A dermoscopic image of a skin lesion; FST I; a female subject in their mid- to late 80s or older:
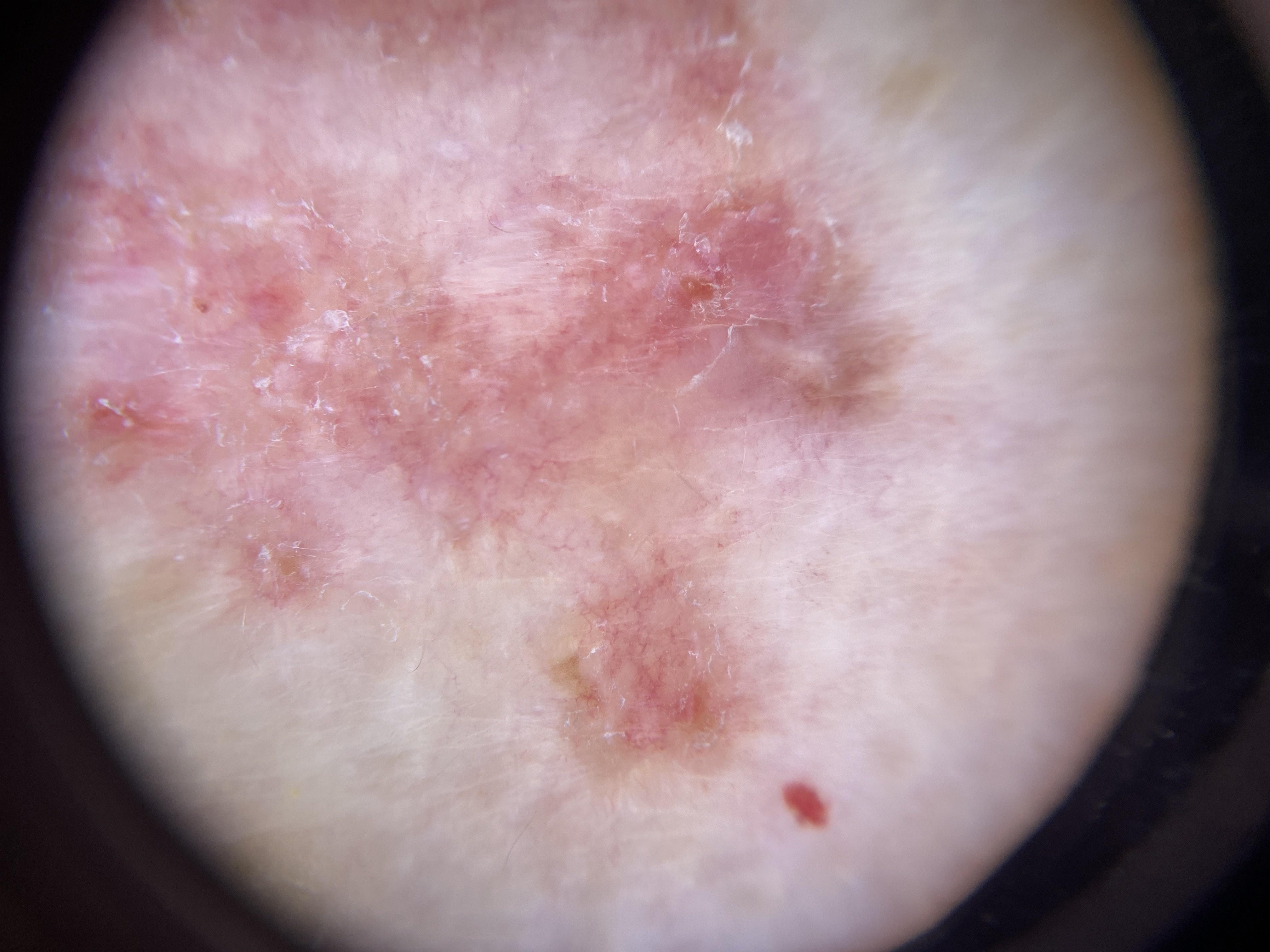Clinical context: The lesion is on an upper extremity. Diagnosis: Histopathologically confirmed as a malignant, adnexal lesion — a basal cell carcinoma.